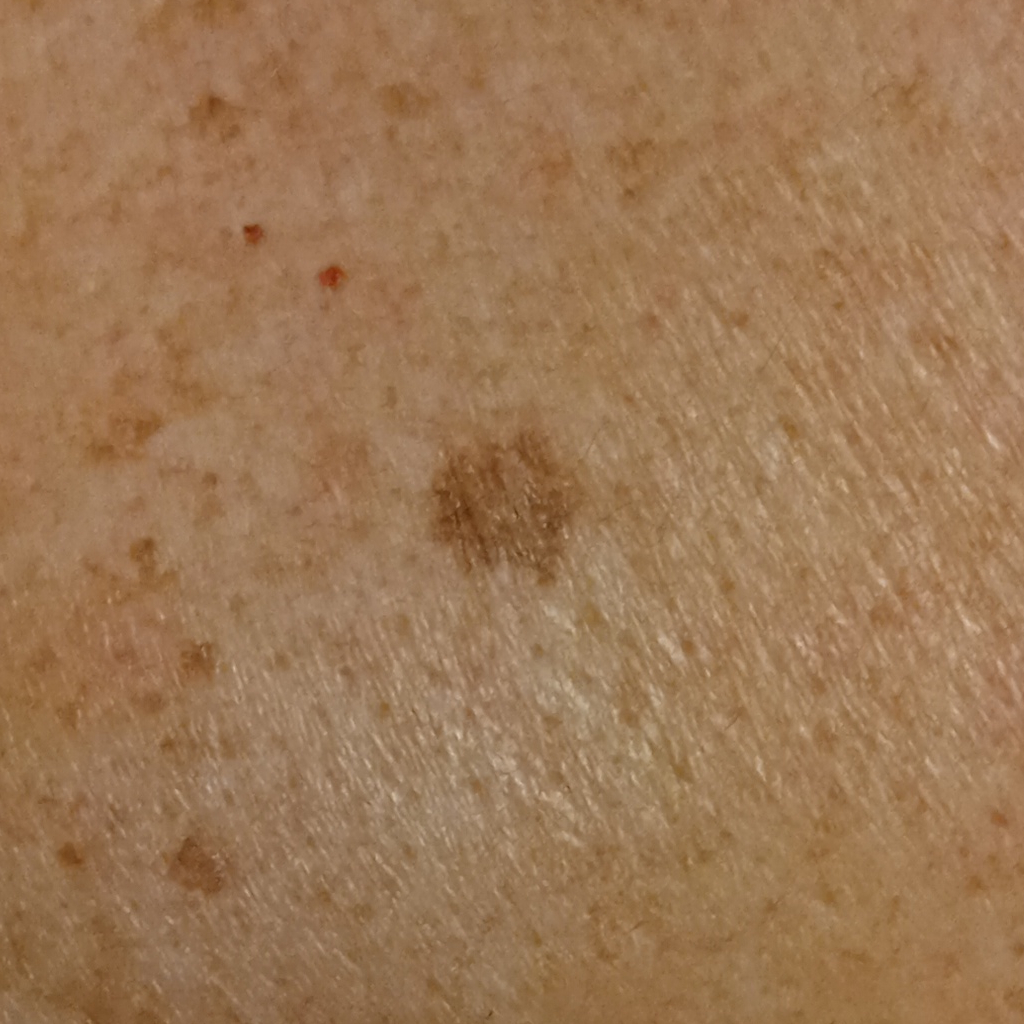The reviewing dermatologists could not reach a confident diagnosis. risk factors — a personal history of cancer, a family history of skin cancer; referral — research study (no referral diagnosis); nevus count — few melanocytic nevi overall; sun reaction — skin reddens with sun exposure; modality — clinical photograph; patient — male, aged 81; body site — the back; size — 8 mm.